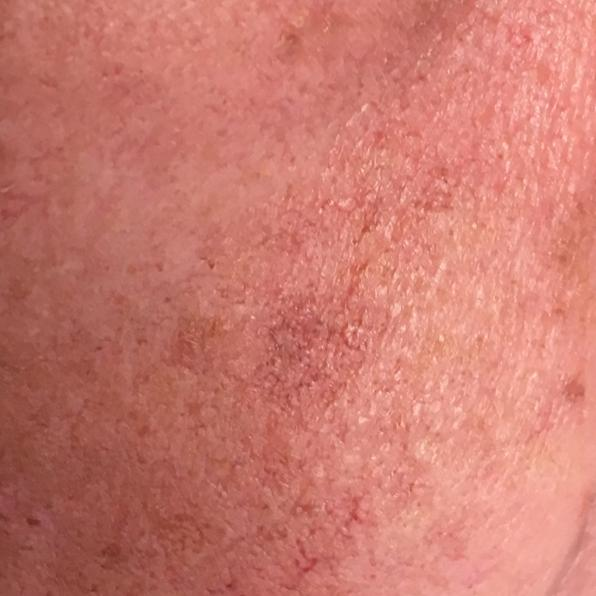Expert review favored an actinic keratosis.